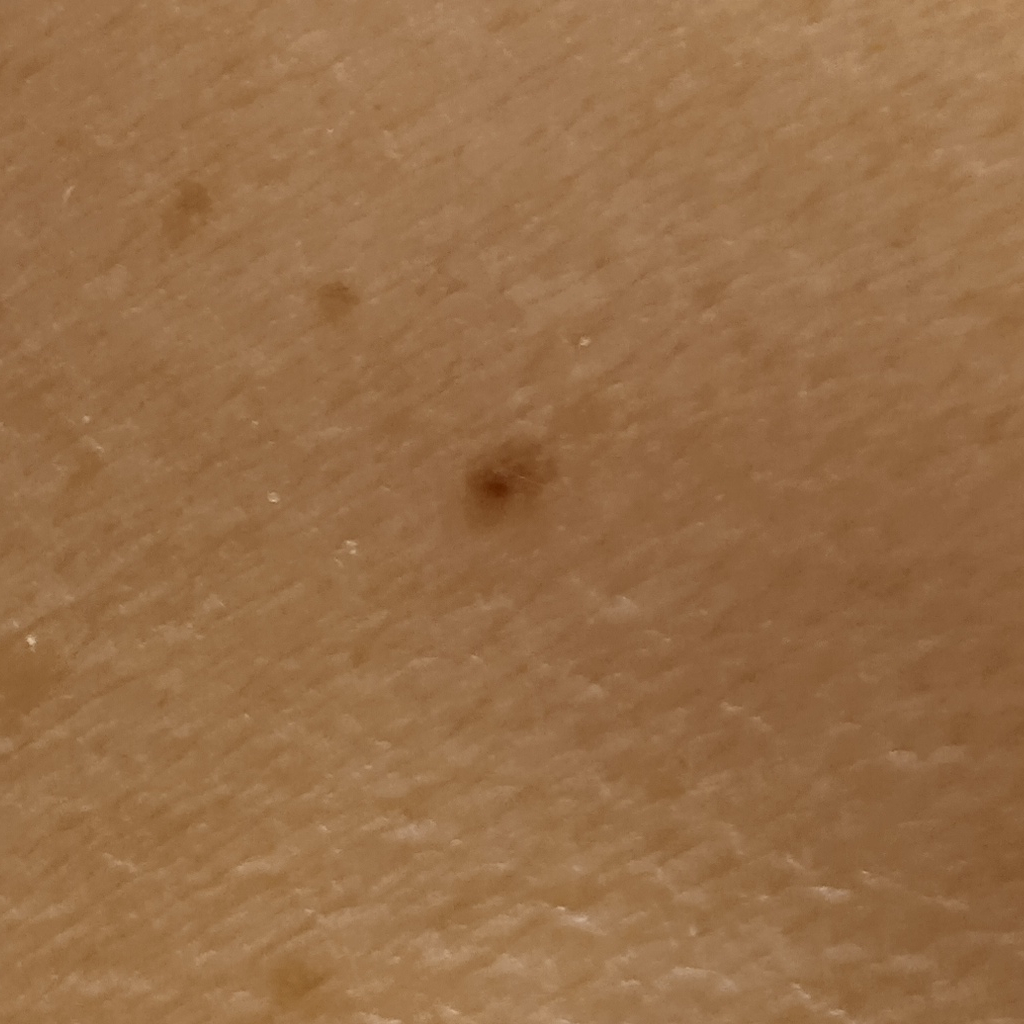referral context = research study (no referral diagnosis)
imaging = clinical photo
subject = female, 81 years of age
location = the back
size = 2.7 mm
assessment = melanocytic nevus (dermatologist consensus)